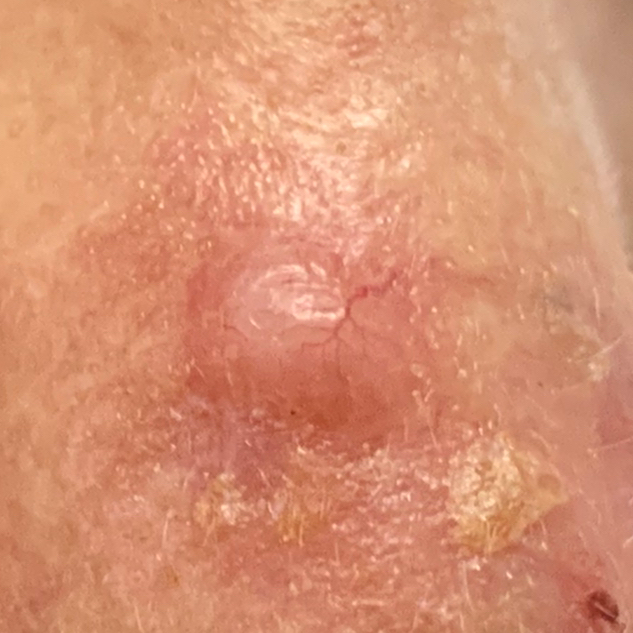Pathology:
On biopsy, the diagnosis was a basal cell carcinoma.